A male subject approximately 70 years of age; dermoscopy of a skin lesion:
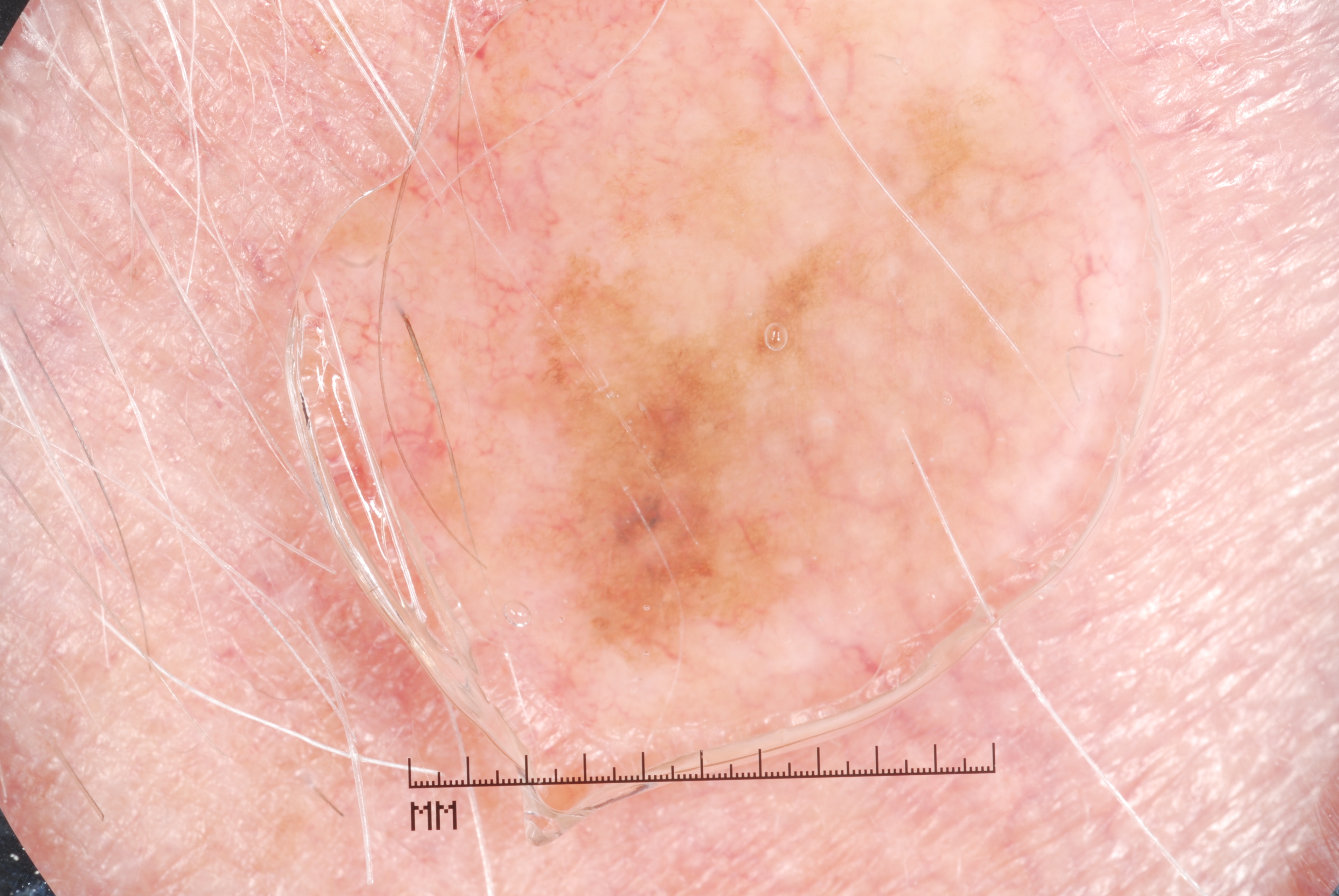{"dermoscopic_features": {"present": ["pigment network"], "absent": ["milia-like cysts", "streaks", "negative network"]}, "lesion_location": {"bbox_xyxy": [473, 161, 929, 691]}, "diagnosis": {"name": "melanoma", "malignancy": "malignant", "lineage": "melanocytic", "provenance": "histopathology"}}